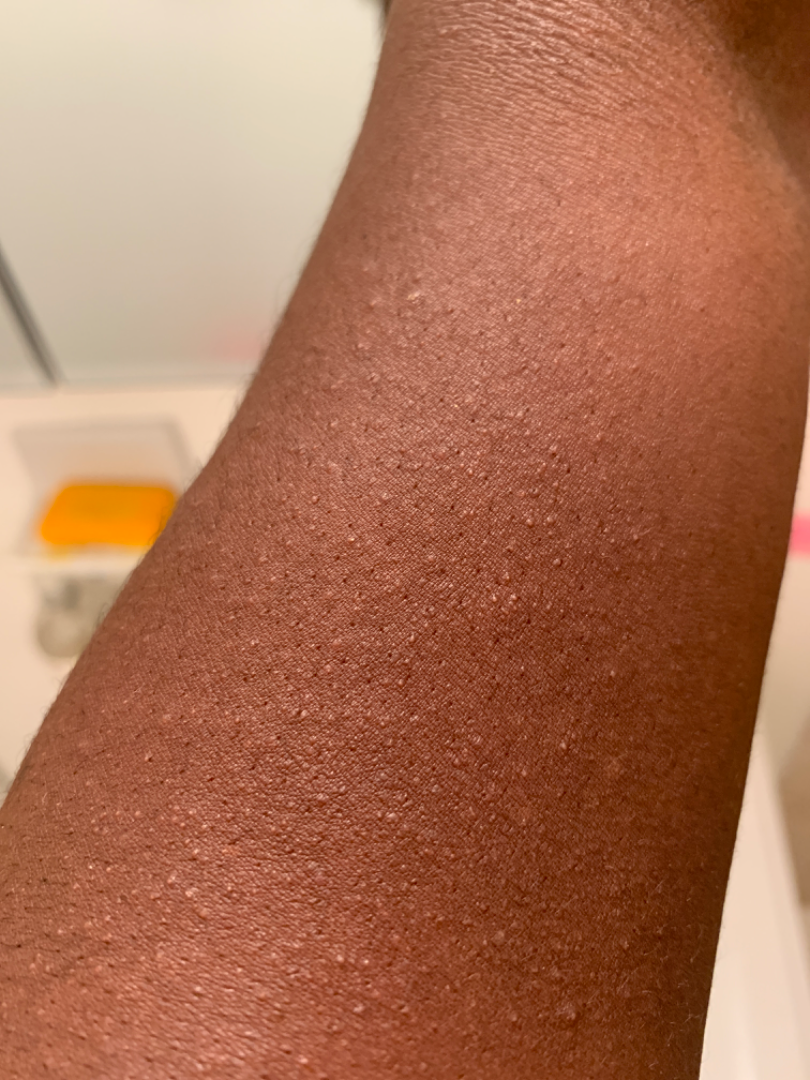Diagnostic features were not clearly distinguishable in this photograph.
The back of the torso and back of the hand are involved.
This image was taken at a distance.